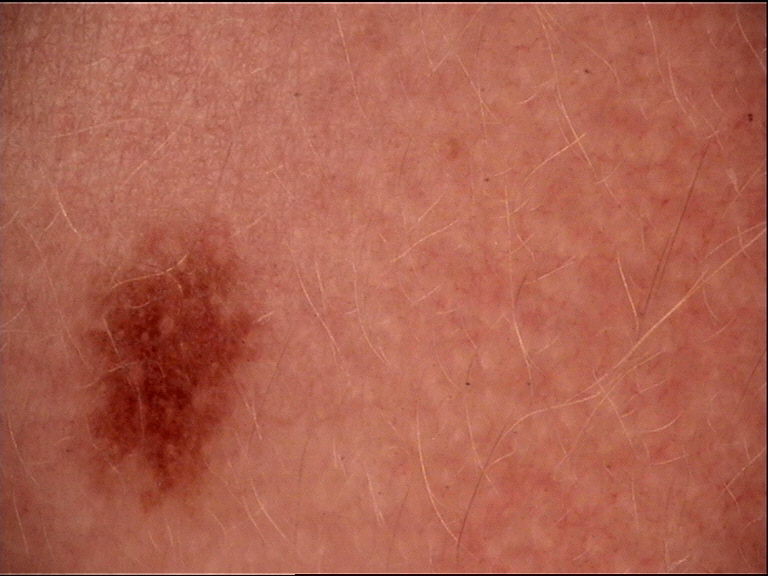Summary: A dermoscopic photograph of a skin lesion. Impression: Classified as a banal lesion — a junctional nevus.